A skin lesion imaged with a dermatoscope.
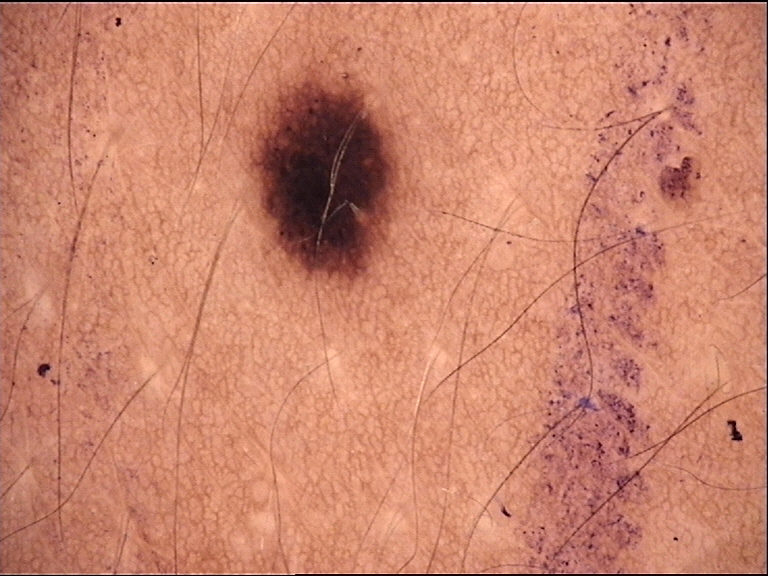{
  "lesion_type": {
    "main_class": "banal",
    "pattern": "junctional"
  },
  "diagnosis": {
    "name": "junctional nevus",
    "code": "jb",
    "malignancy": "benign",
    "super_class": "melanocytic",
    "confirmation": "expert consensus"
  }
}